The patient was assessed as Fitzpatrick skin type II. By history, pesticide exposure. A smartphone photograph of a skin lesion. A female subject in their 60s — 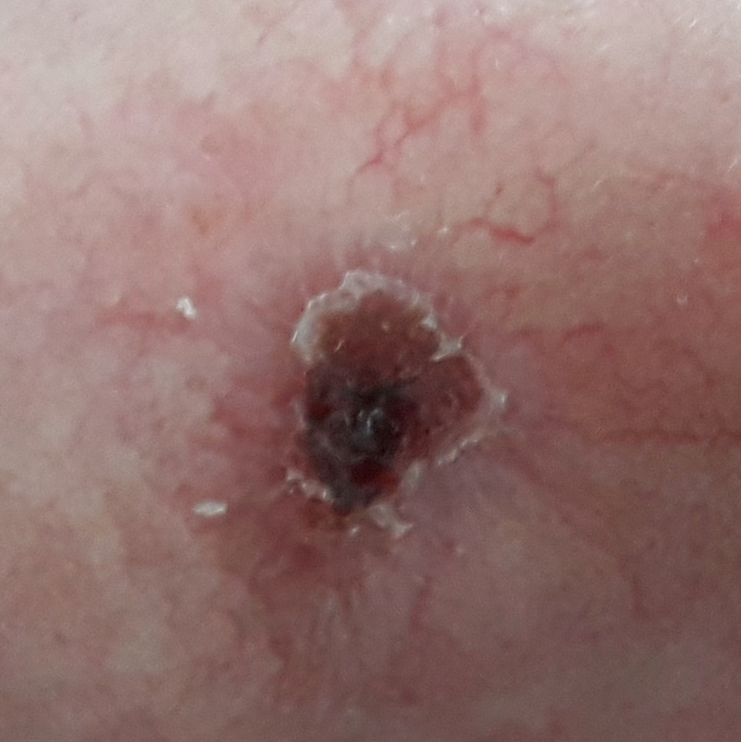The lesion is located on the nose. Measuring about 5 × 3 mm. The patient describes that the lesion is elevated, has changed, has bled, has grown, and itches, but does not hurt. Confirmed on histopathology as a basal cell carcinoma.